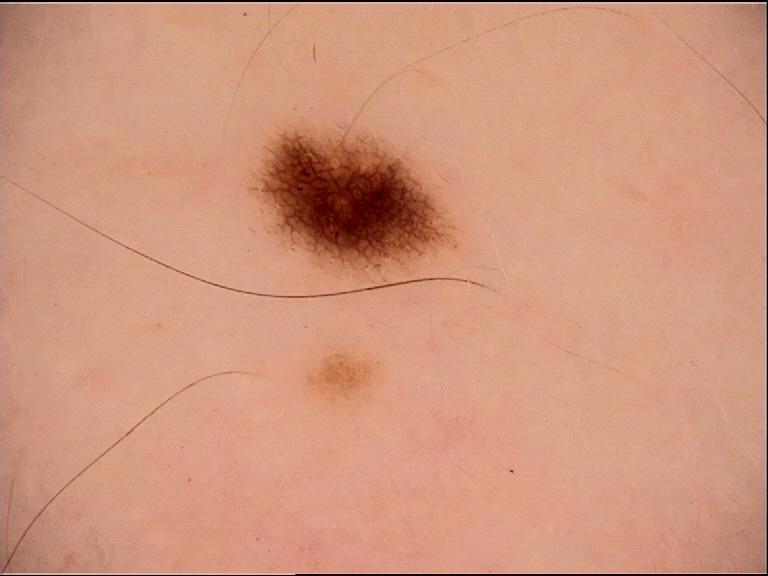Case:
A dermoscopy image of a single skin lesion.
Conclusion:
The diagnostic label was a benign lesion — a dysplastic junctional nevus.